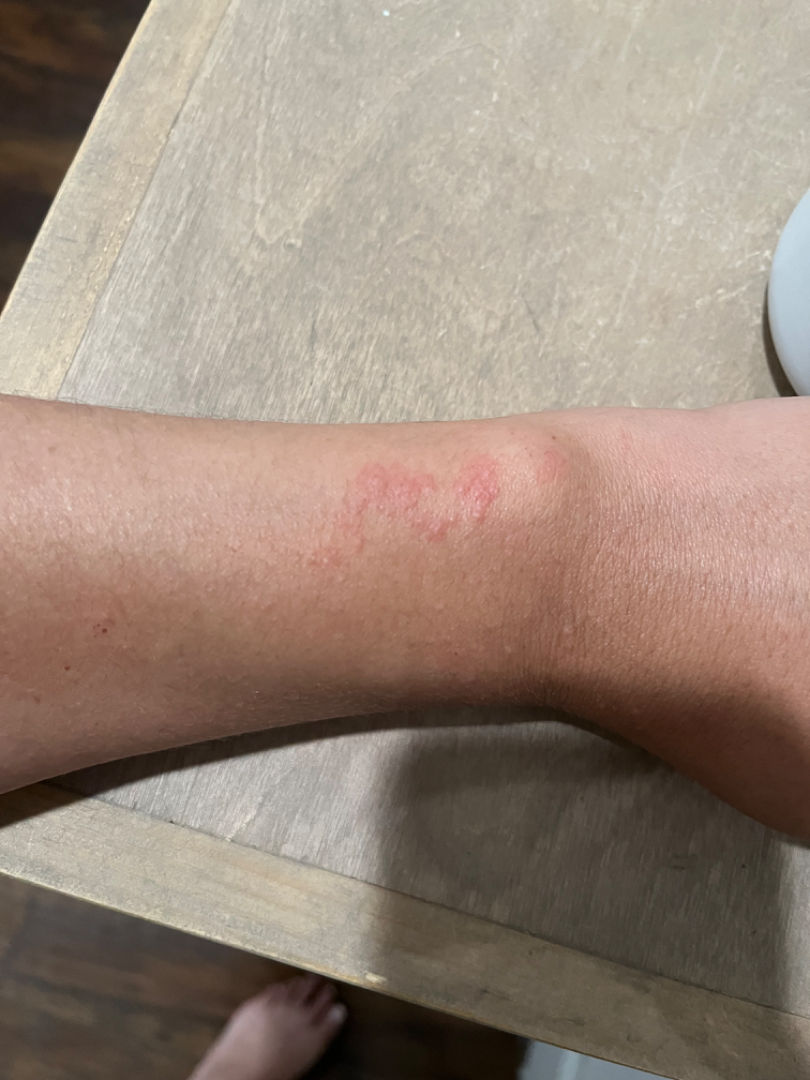The affected area is the arm.
The photograph is a close-up of the affected area.
Most likely Allergic Contact Dermatitis; possibly Irritant Contact Dermatitis.